A dermoscopic close-up of a skin lesion.
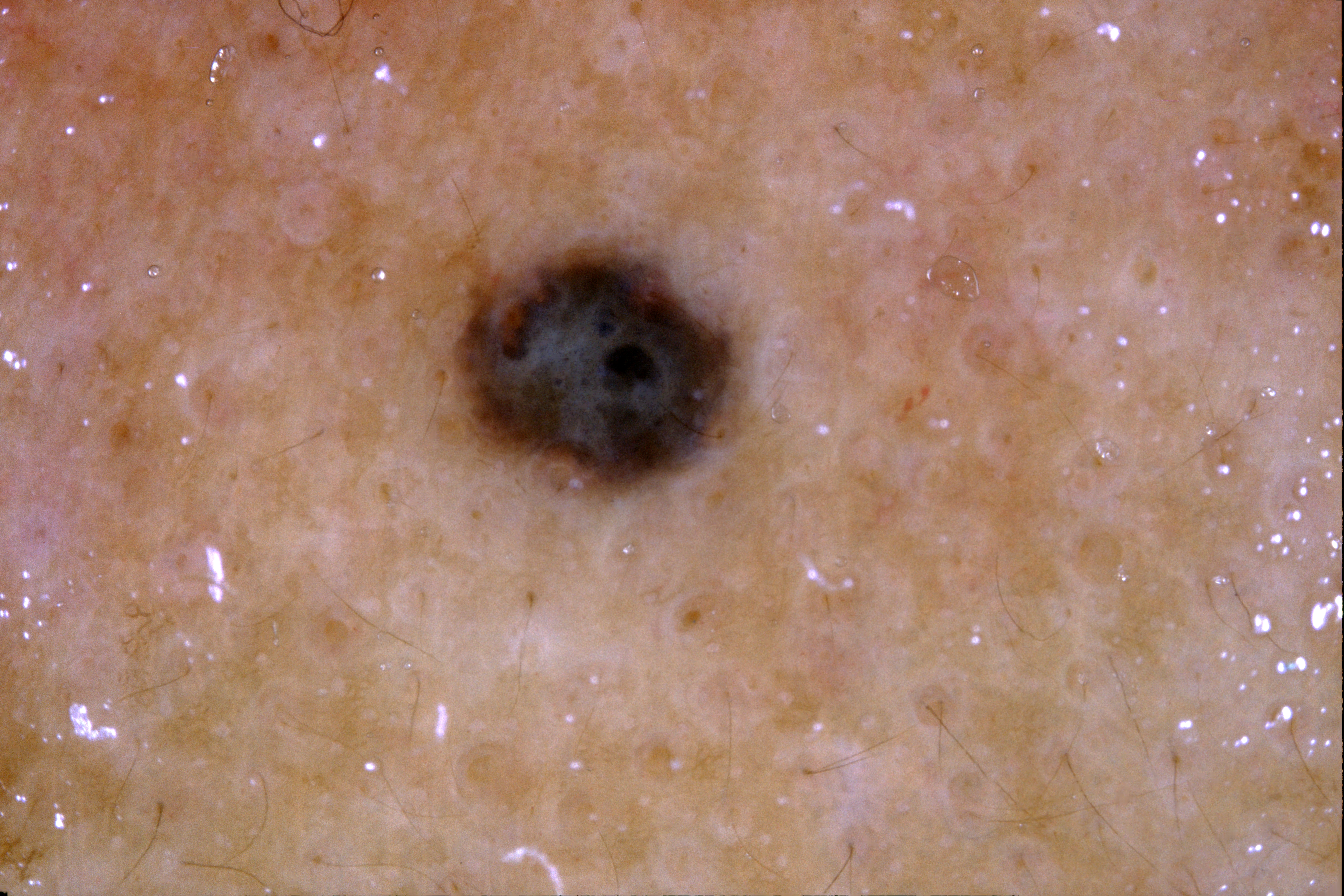size = ~4% of the field | lesion bbox = bbox=[454, 241, 741, 495] | absent dermoscopic features = negative network, pigment network, milia-like cysts, and streaks | diagnosis = a melanocytic nevus.